Referred with a clinical suspicion of basal cell carcinoma; by self-report, a personal history of cancer, a personal history of skin cancer, and no family history of skin cancer; a clinical photograph of a skin lesion; the patient says their skin tans without first burning:
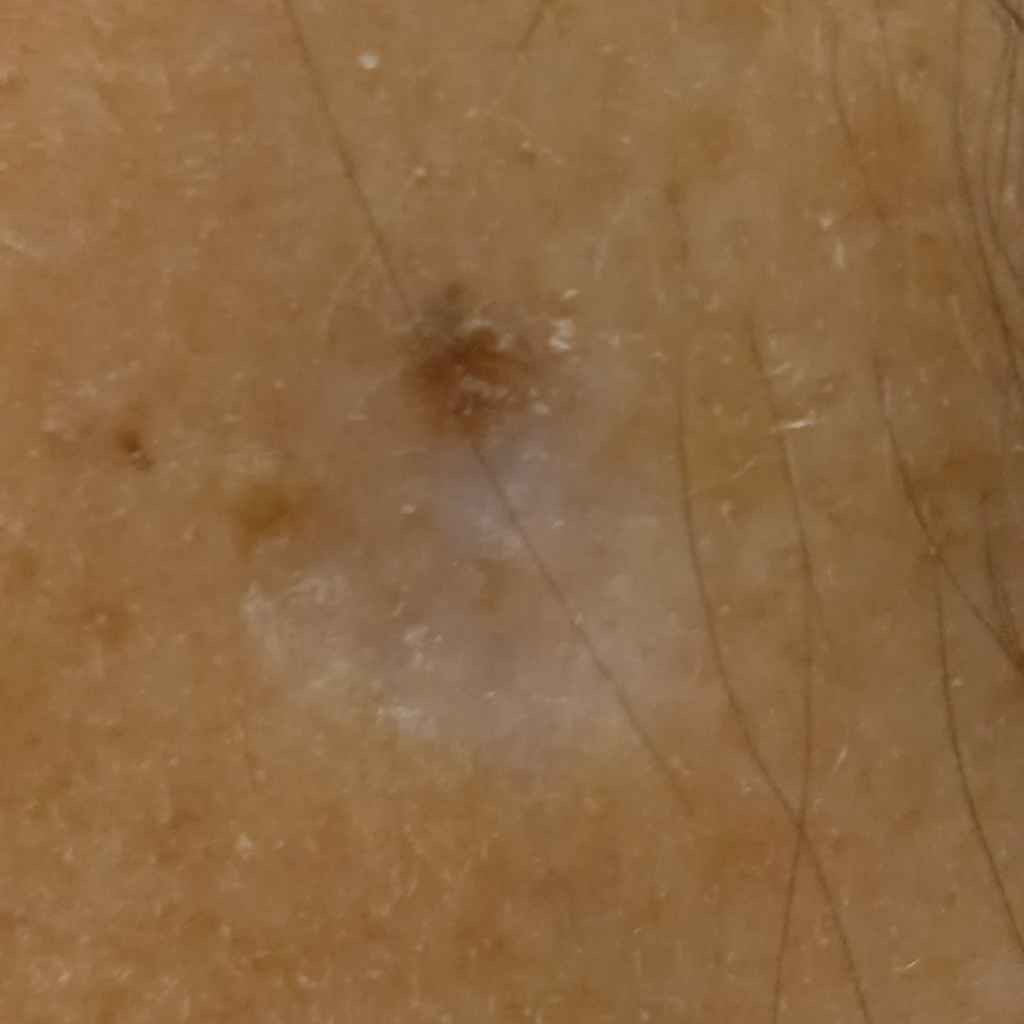{
  "lesion_location": "the face",
  "lesion_size": {
    "diameter_mm": 6.6
  },
  "diagnosis": {
    "name": "basal cell carcinoma",
    "malignancy": "malignant",
    "procedure": "excision",
    "tumor_thickness_mm": 1.0
  }
}